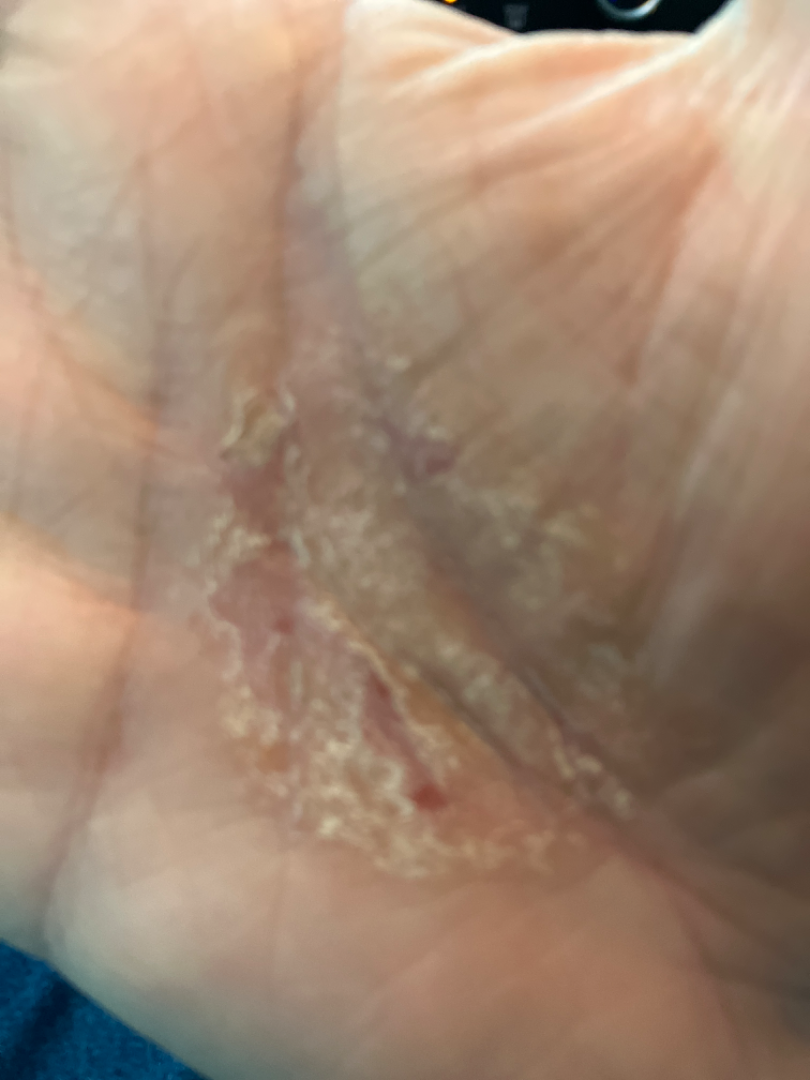Clinical context: Self-categorized by the patient as a rash. A close-up photograph. Reported lesion symptoms include bothersome appearance. Present for three to twelve months. Assessment: The primary impression is Psoriasis; the differential also includes Eczema; an alternative is Allergic Contact Dermatitis.